This is a close-up image; the lesion involves the leg; male patient, age 50–59 — 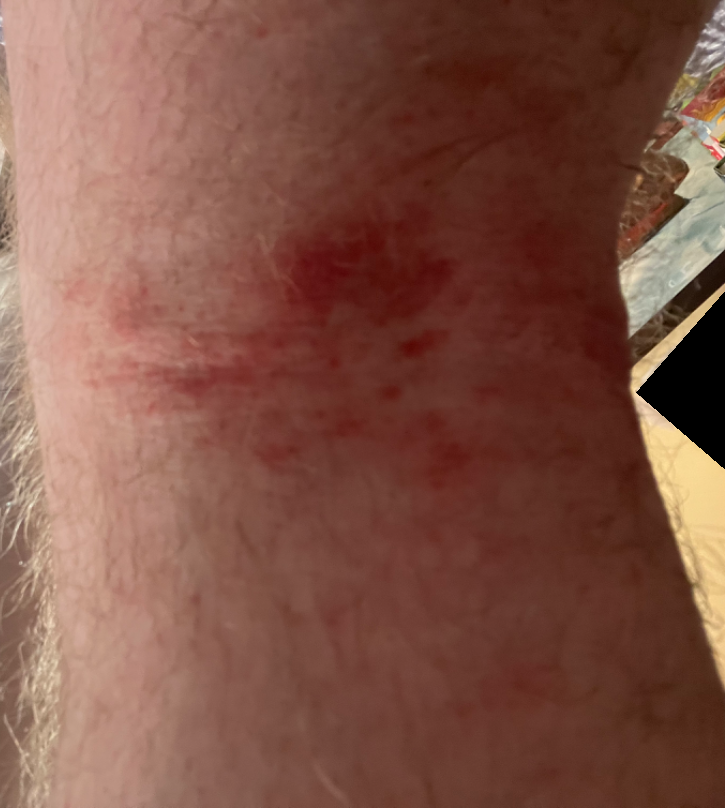Patient information: Skin tone: Fitzpatrick skin type II. Texture is reported as raised or bumpy. The lesion is associated with itching, burning and bothersome appearance. The patient reports the condition has been present for one to four weeks. No constitutional symptoms were reported. The patient described the issue as a rash. Review: Most consistent with Eczema; the differential also includes Allergic Contact Dermatitis; also consider Irritant Contact Dermatitis; less probable is Abrasion, scrape, or scab; less likely is Acute dermatitis, NOS.